No associated systemic symptoms reported; symptoms reported: itching and bothersome appearance; the condition has been present for more than one year; the patient is 30–39, male; self-categorized by the patient as skin that appeared healthy to them; located on the palm and back of the hand; an image taken at a distance:
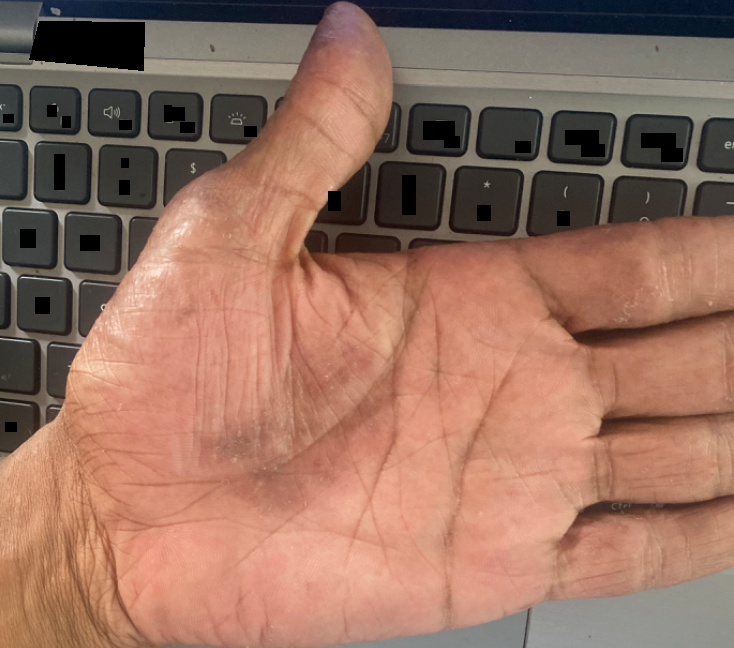Q: What is the dermatologist's impression?
A: the differential is split between Tinea; Keratoderma; and Chronic dermatitis, NOS